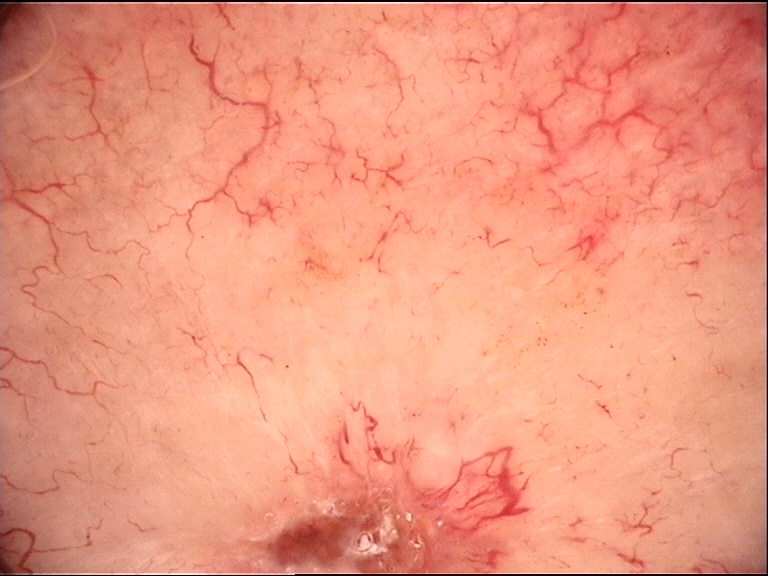Findings:
* diagnosis: basal cell carcinoma (biopsy-proven)